The leg is involved · the contributor is a female aged 18–29 · the photograph was taken at an angle: 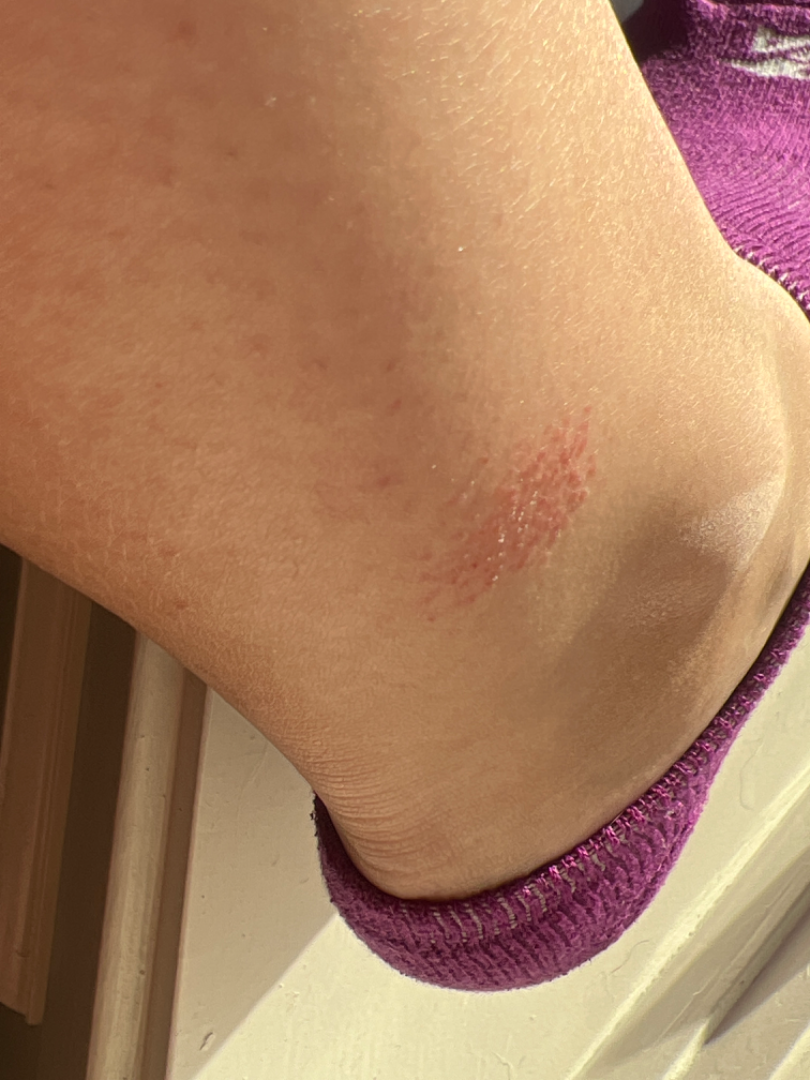differential:
  leading:
    - Eczema
  considered:
    - Irritant Contact Dermatitis
  unlikely:
    - Acute dermatitis, NOS
    - Tinea
    - Allergic Contact Dermatitis